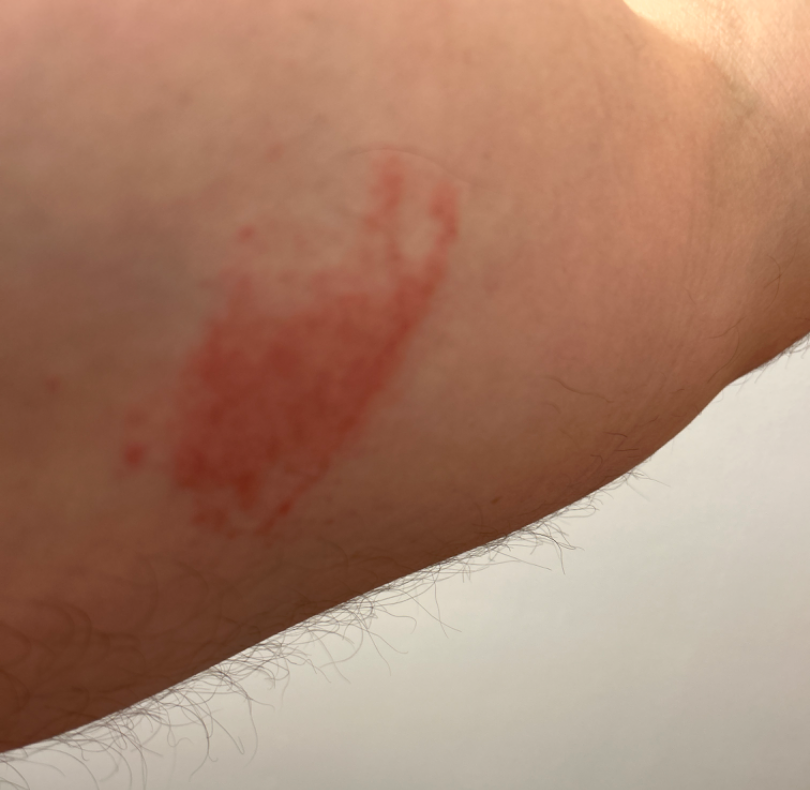<report>
  <assessment>ungradable on photographic review</assessment>
  <patient>male, age 40–49</patient>
  <body_site>front of the torso, leg, arm, back of the hand</body_site>
  <shot_type>close-up</shot_type>
</report>